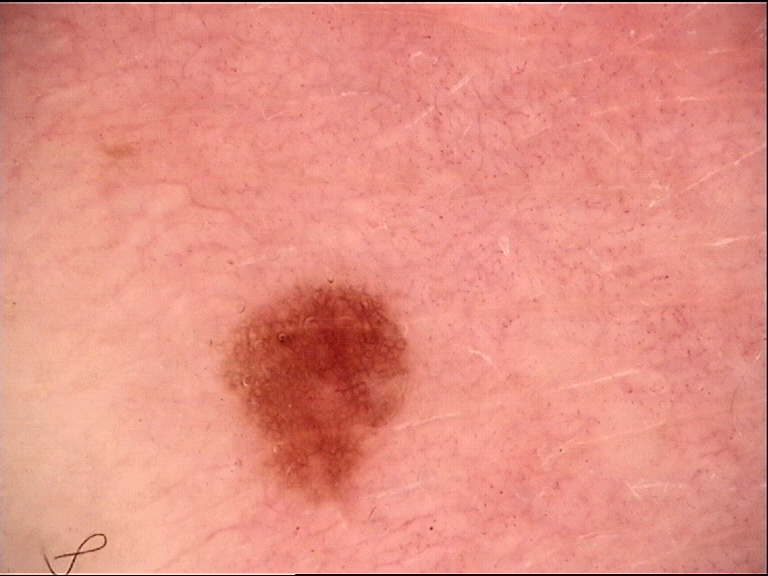{
  "diagnosis": {
    "name": "junctional nevus",
    "code": "jb",
    "malignancy": "benign",
    "super_class": "melanocytic",
    "confirmation": "expert consensus"
  }
}